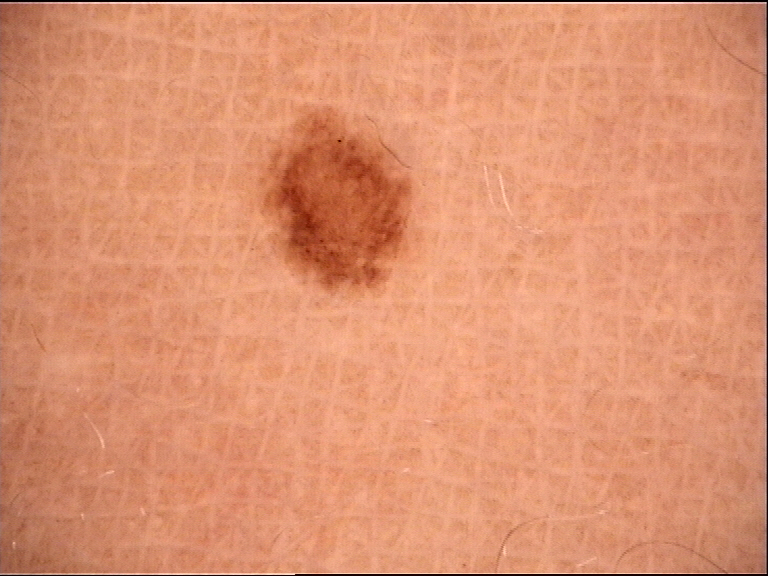label = dysplastic junctional nevus (expert consensus).